The photograph is a close-up of the affected area — 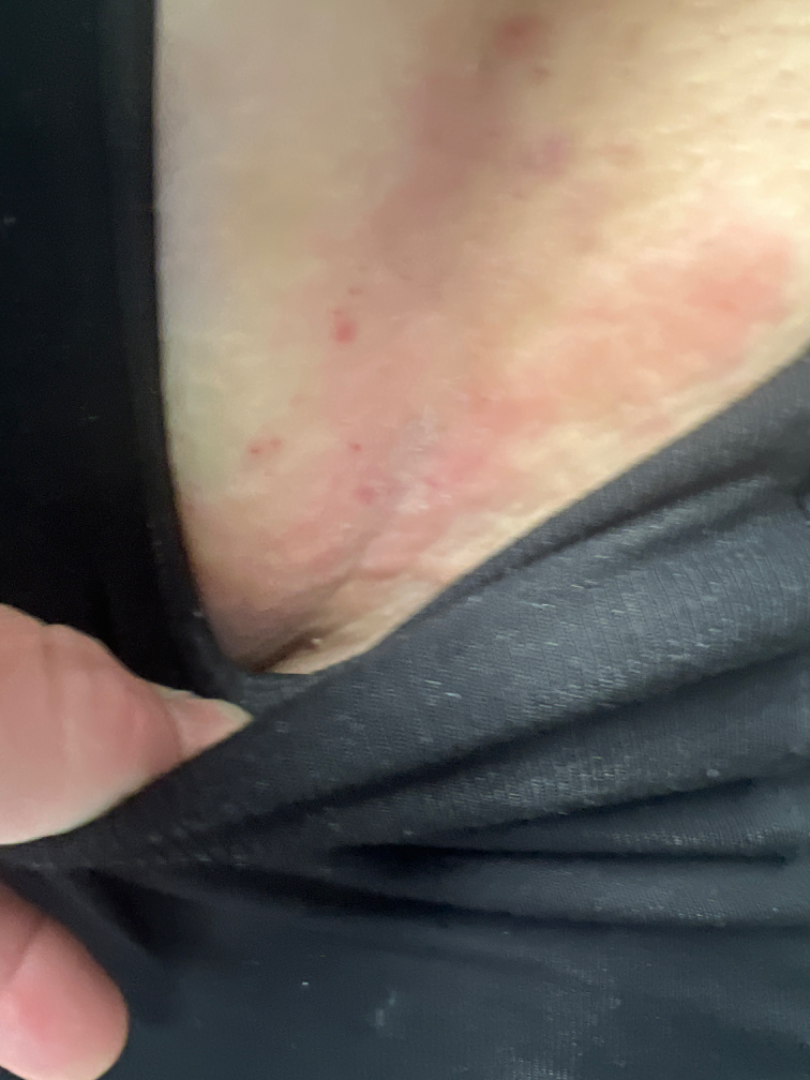- assessment — could not be assessed